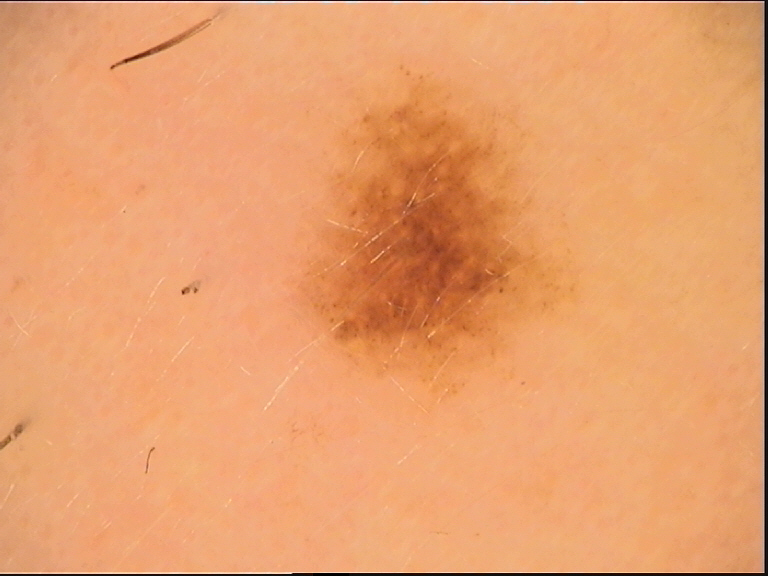image type: dermoscopy | assessment: dysplastic compound nevus (expert consensus).